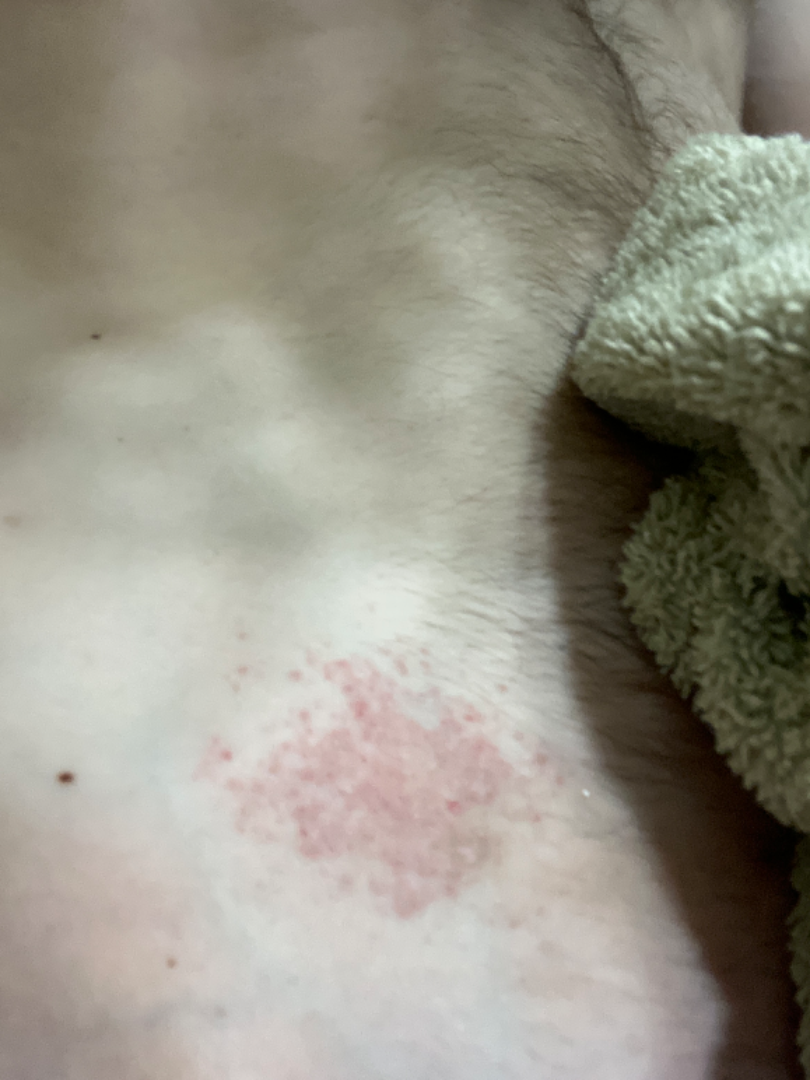No relevant systemic symptoms.
The patient considered this a rash.
The lesion is described as rough or flaky and raised or bumpy.
A close-up photograph.
Present for one to four weeks.
Located on the front of the torso.
The contributor is a male aged 18–29.
The leading consideration is Allergic Contact Dermatitis; also consider Tinea; possibly Eczema.